The contributor reports itching, pain and enlargement; the lesion involves the sole of the foot, top or side of the foot, palm and back of the hand; male contributor, age 18–29; self-categorized by the patient as a rash; reported duration is about one day; the photo was captured at an angle: 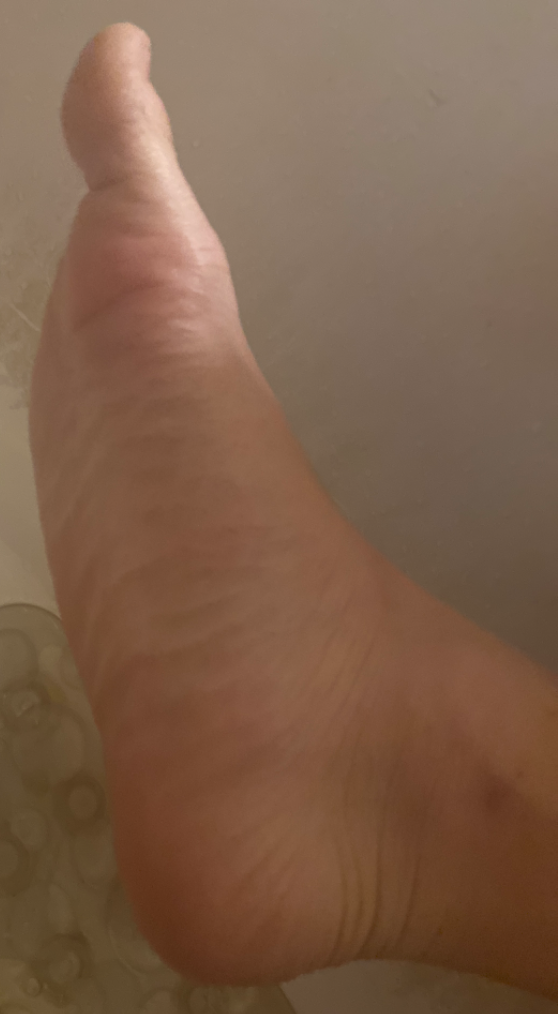Q: What was the assessment?
A: no skin condition identified